The patient is a male about 35 years old. A dermoscopic image of a skin lesion:
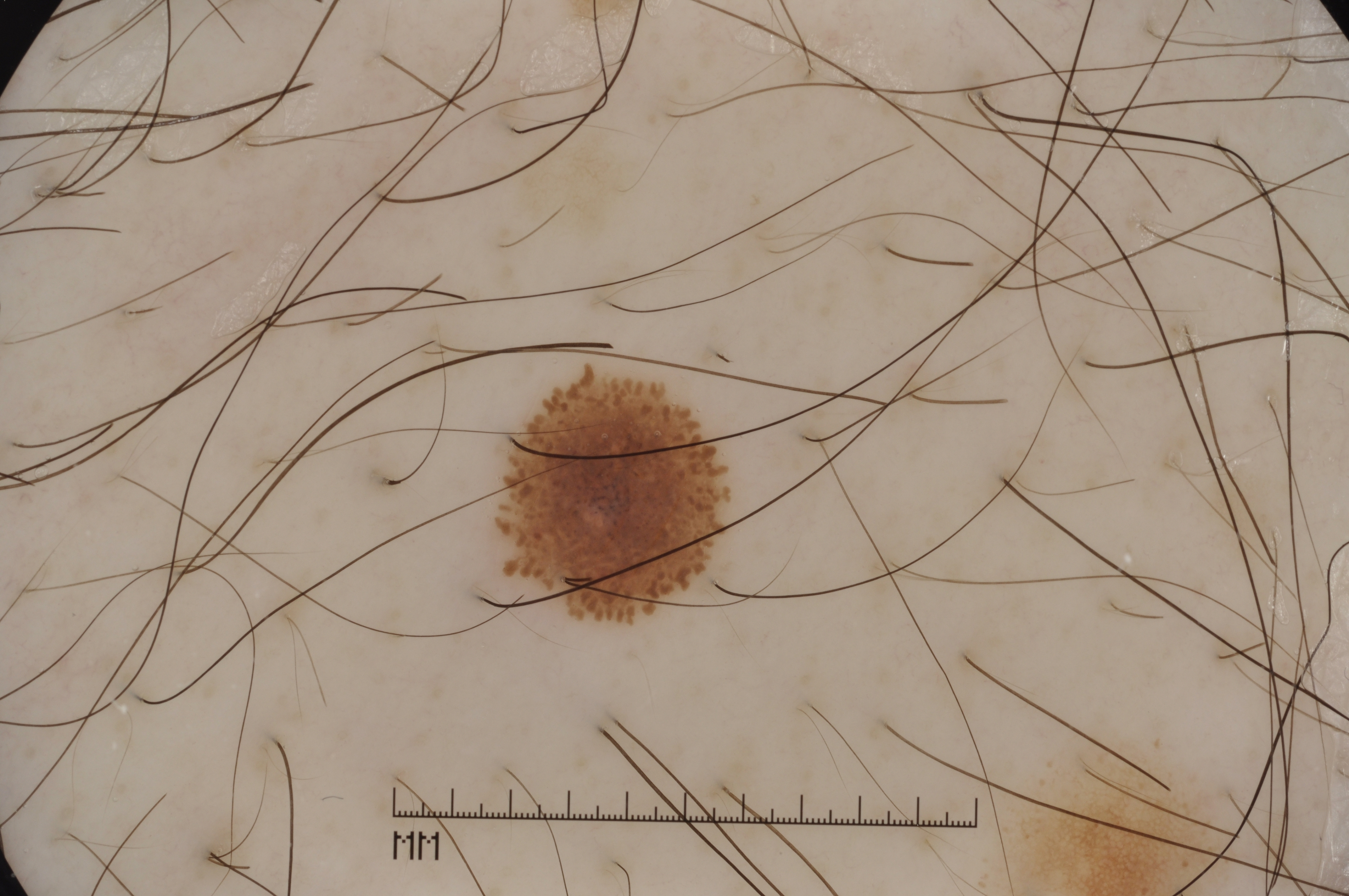{"dermoscopic_features": {"present": ["streaks", "negative network"], "absent": ["pigment network", "milia-like cysts"]}, "lesion_location": {"bbox_xyxy": [506, 378, 727, 616]}, "lesion_extent": {"approx_field_fraction_pct": 3}, "diagnosis": {"name": "melanocytic nevus", "malignancy": "benign", "lineage": "melanocytic", "provenance": "clinical"}}